A dermatoscopic image of a skin lesion:
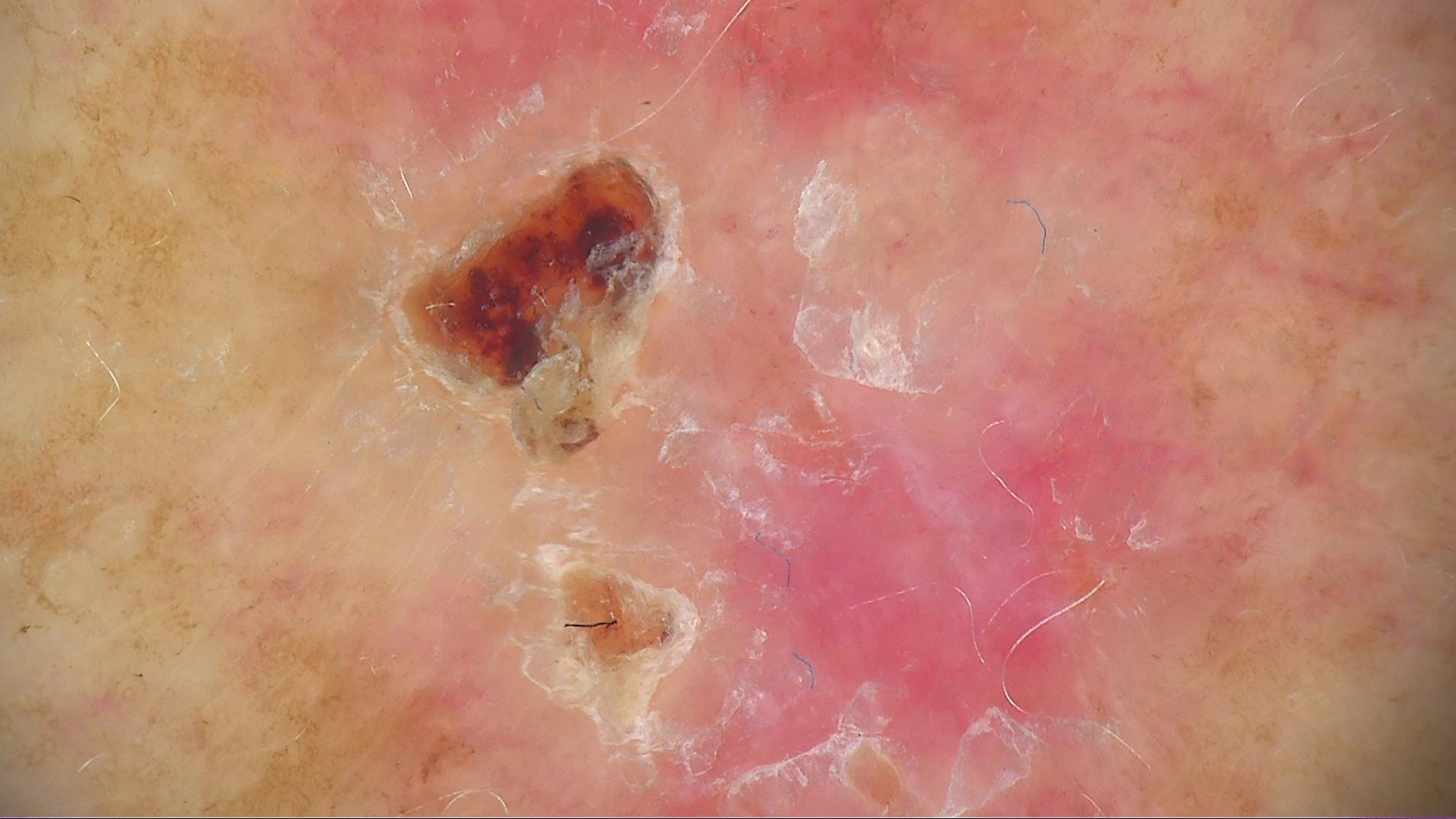Summary: The architecture is that of a keratinocytic lesion. Conclusion: Biopsy-confirmed as a basal cell carcinoma.